A female patient approximately 60 years of age; a dermoscopic image of a skin lesion: 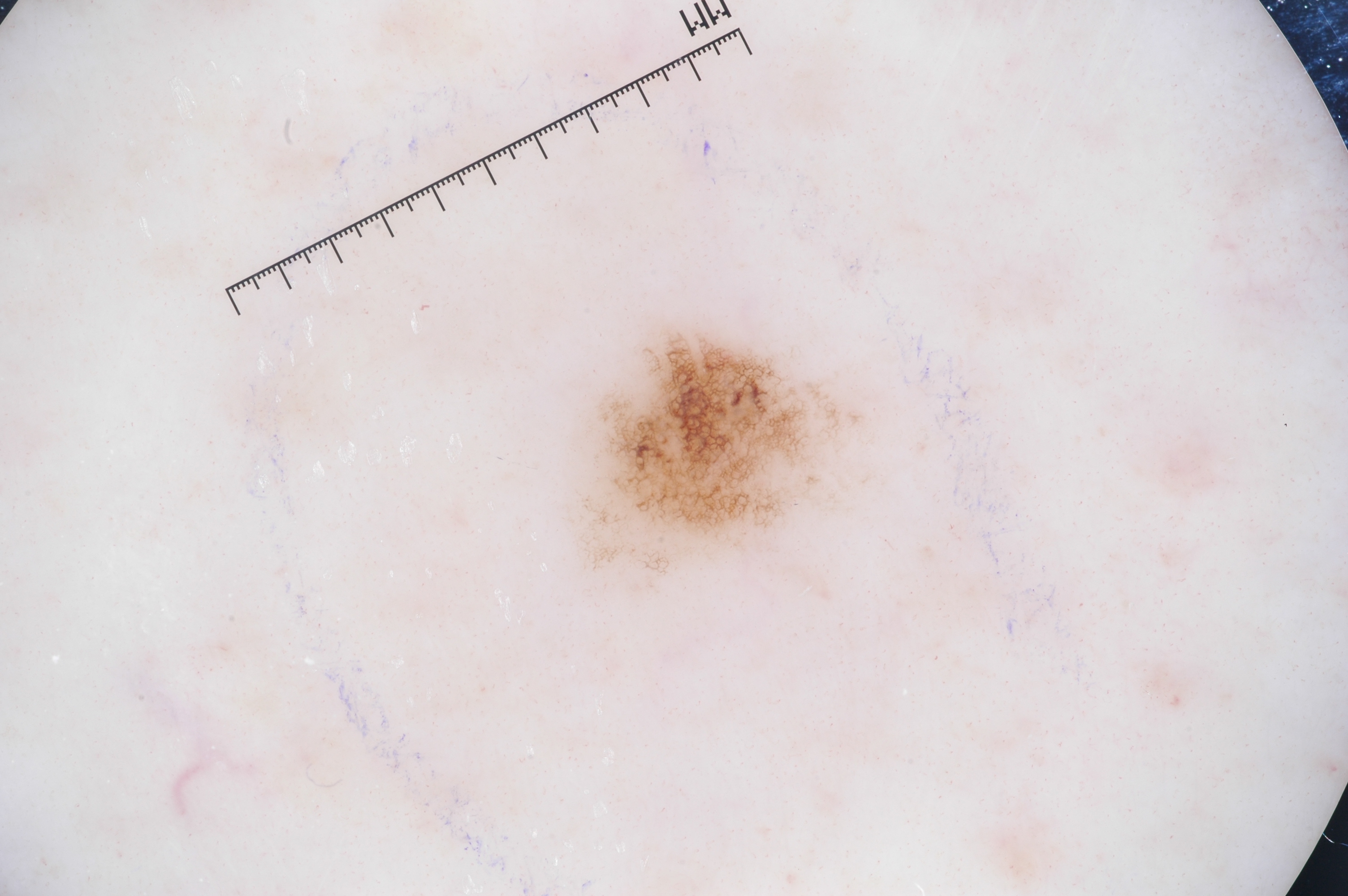<record>
  <dermoscopic_features>
    <present>pigment network</present>
    <absent>milia-like cysts, streaks, negative network</absent>
  </dermoscopic_features>
  <lesion_extent>small</lesion_extent>
  <lesion_location>
    <bbox_xyxy>590, 329, 853, 574</bbox_xyxy>
  </lesion_location>
  <diagnosis>
    <name>melanocytic nevus</name>
    <malignancy>benign</malignancy>
    <lineage>melanocytic</lineage>
    <provenance>clinical</provenance>
  </diagnosis>
</record>